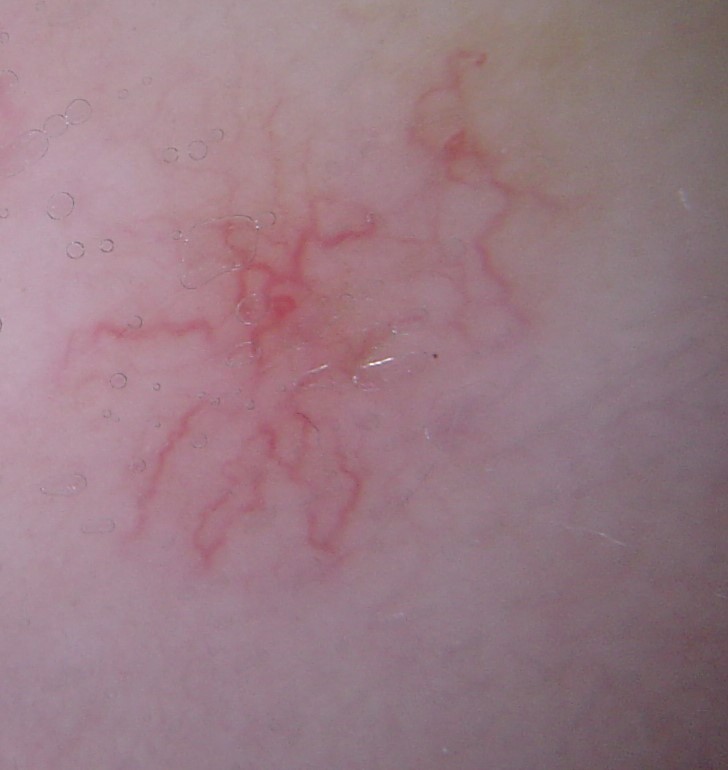imaging = dermatoscopy; classification = vascular; label = spider angioma (expert consensus).